The photograph was taken at an angle · the patient is a male aged 18–29 · the affected area is the front of the torso:
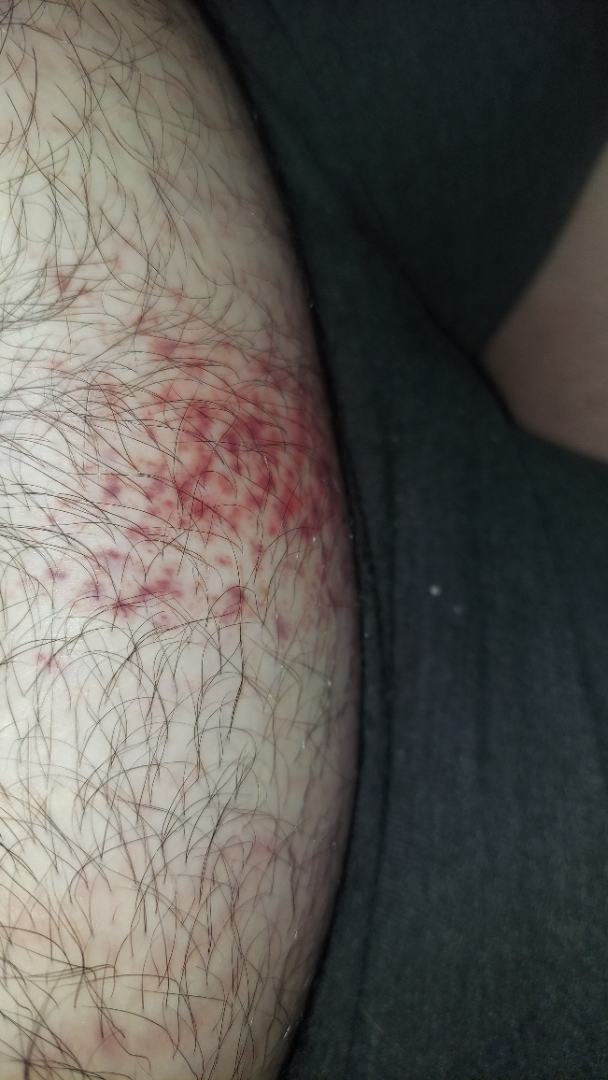assessment: indeterminate from the photograph